The lesion involves the back of the torso and leg; the photo was captured at a distance: 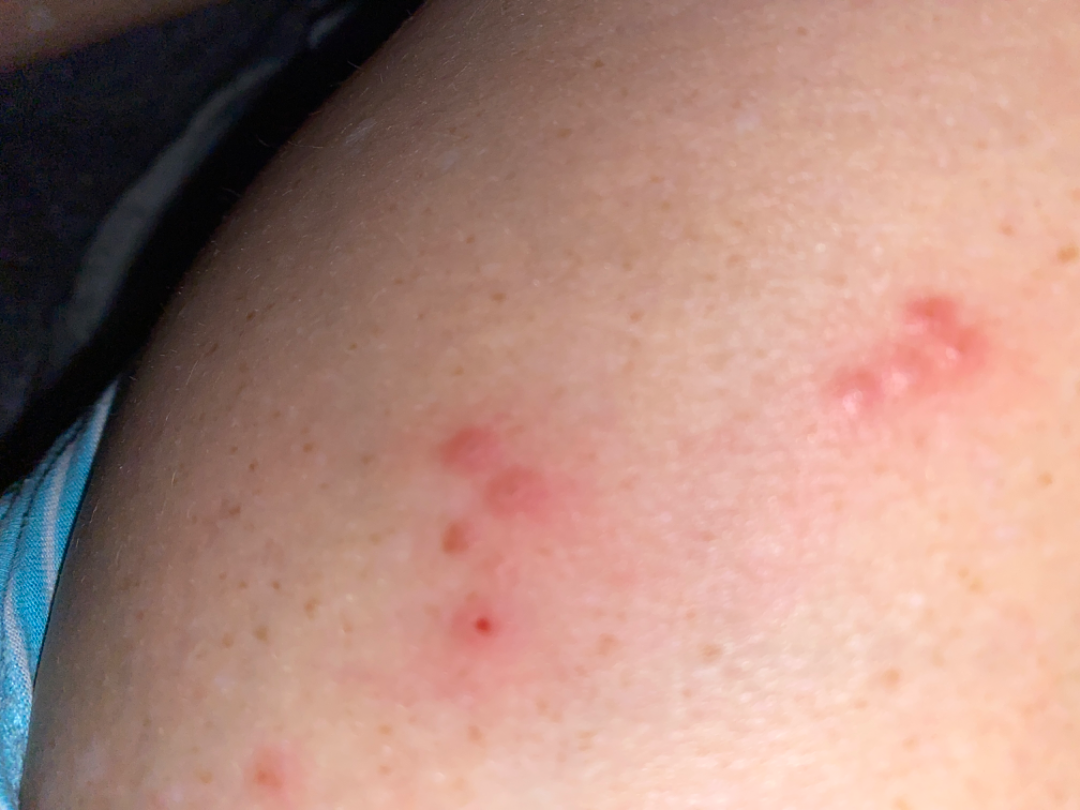Findings:
- assessment · indeterminate from the photograph